Present for more than one year. Female patient, age 50–59. The patient notes the lesion is rough or flaky. This image was taken at an angle. The patient considered this a rash. The leg is involved. Reported lesion symptoms include enlargement and bothersome appearance.
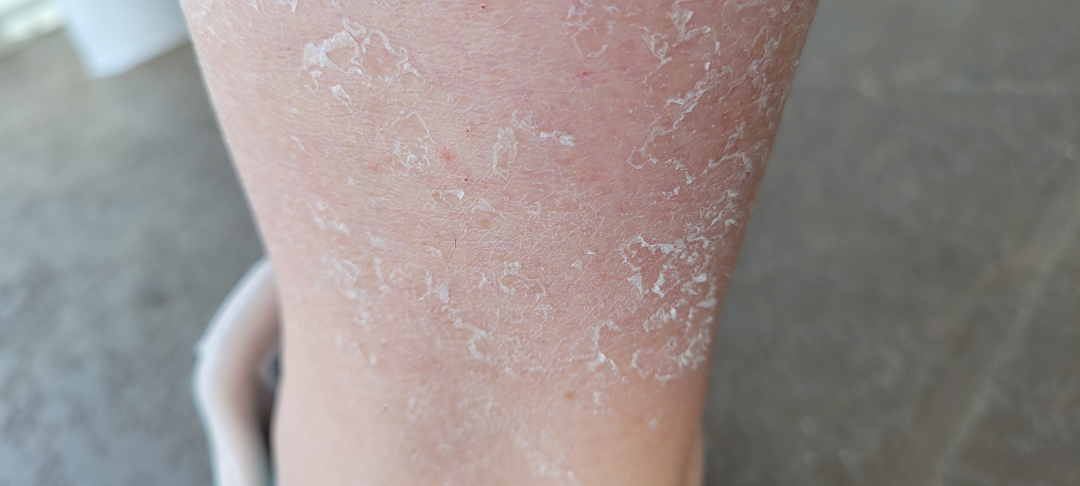Notes:
* differential: the favored diagnosis is Xerosis; an alternative is Eczema; a more distant consideration is post-sunburn peeling/superficial desquamation